A patient aged 73:
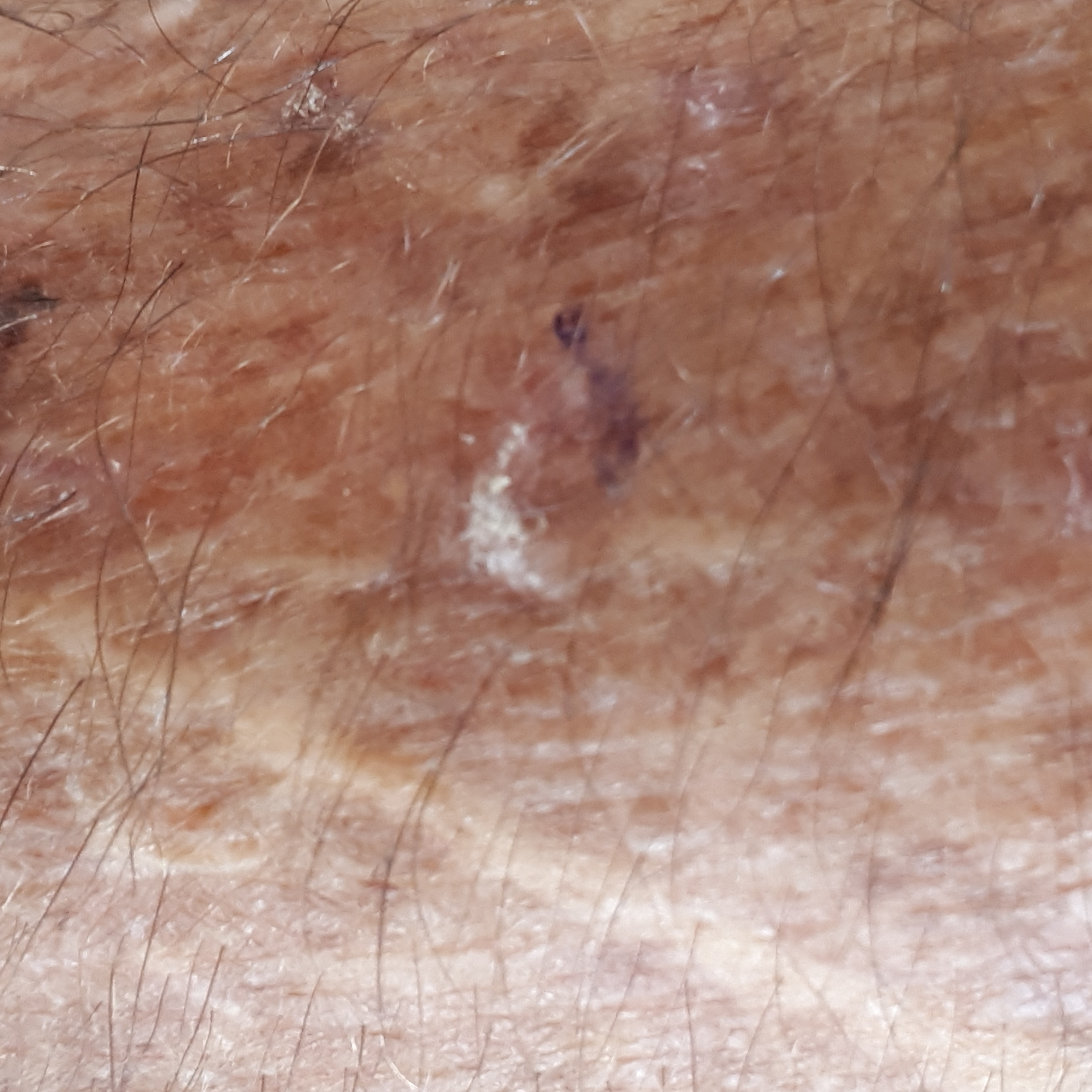location=a forearm | reported symptoms=itching | diagnosis=actinic keratosis (clinical consensus).